A dermatoscopic image of a skin lesion:
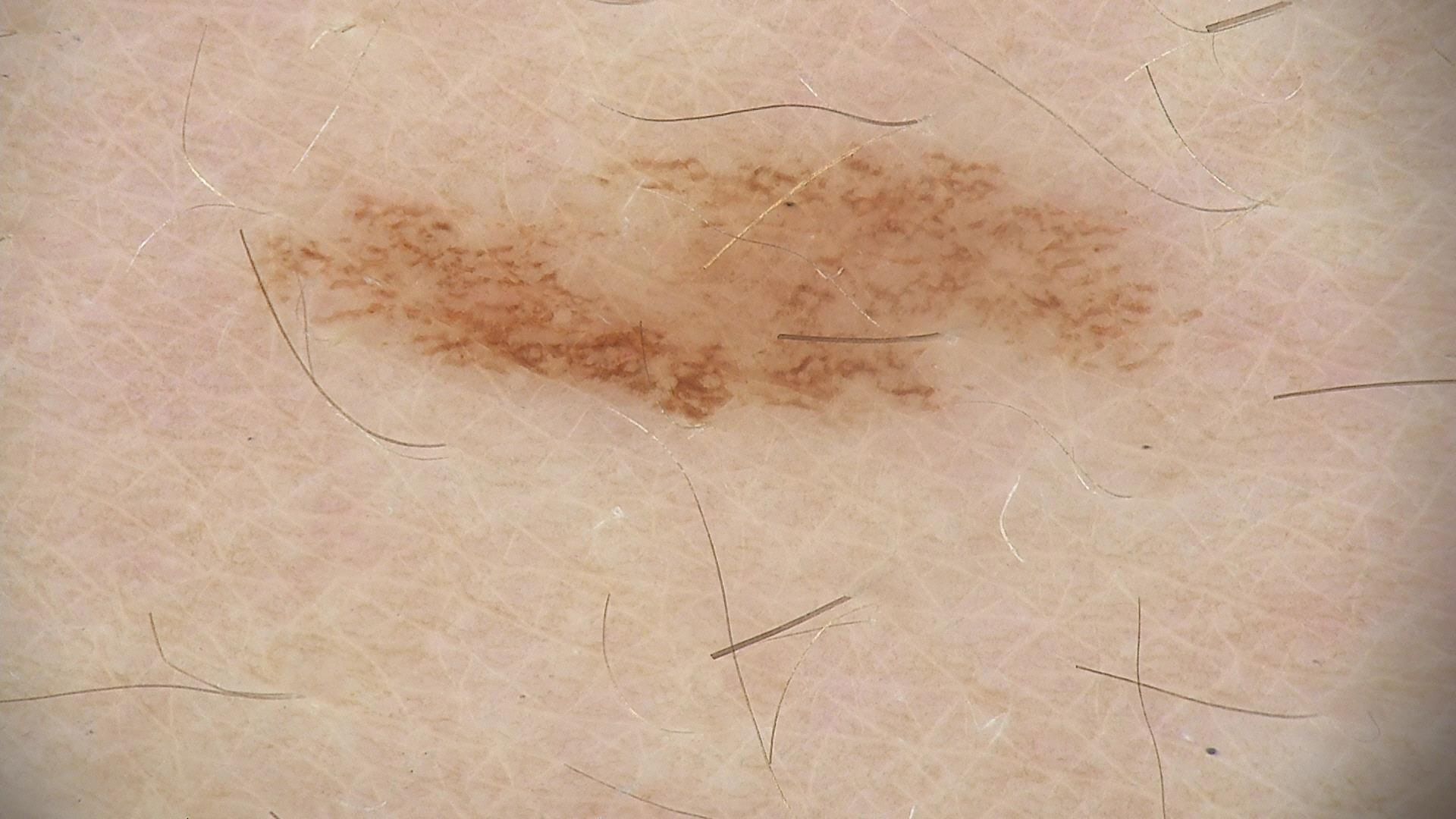The diagnostic label was a dysplastic junctional nevus.